The patient was assessed as Fitzpatrick skin type III · a female subject in their mid-40s · a clinical photograph showing a skin lesion.
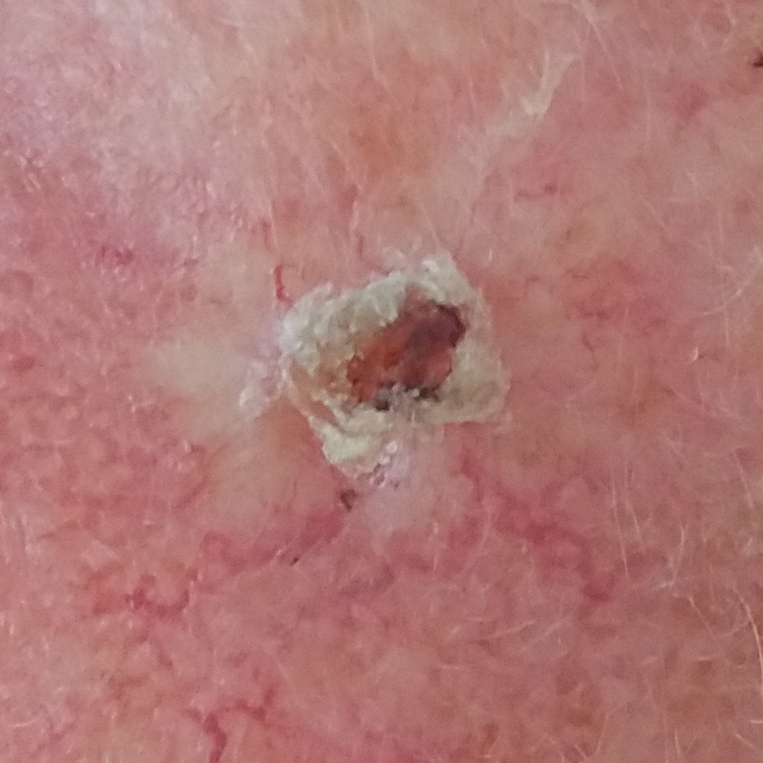The lesion was found on the face. The lesion measures 5 × 5 mm. By the patient's account, the lesion itches, is elevated, has grown, and has bled. On biopsy, the diagnosis was a basal cell carcinoma.